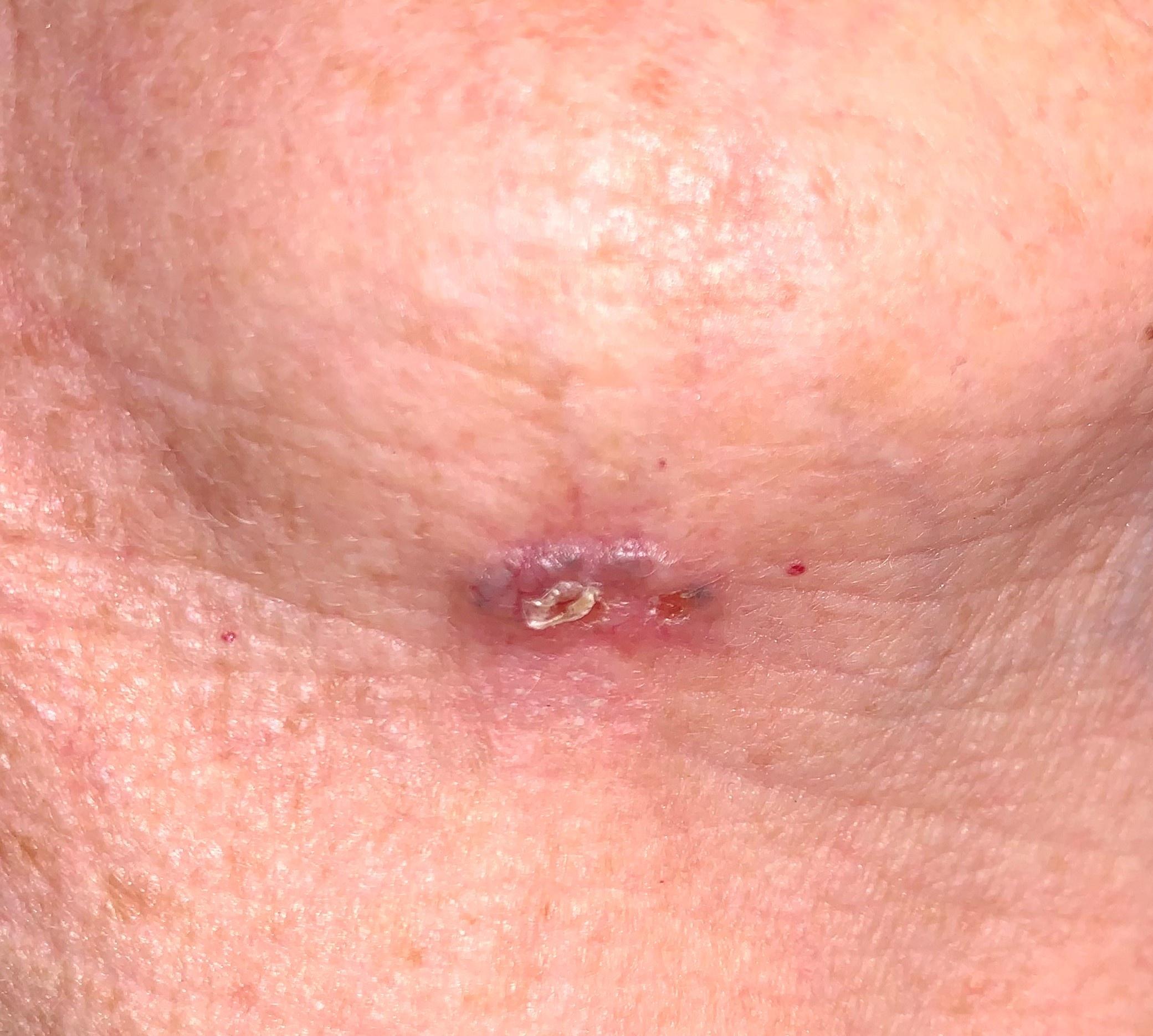<case>
<patient>
<age_approx>75</age_approx>
<sex>female</sex>
</patient>
<image>clinical overview photograph</image>
<lesion_location>
<region>the head or neck</region>
</lesion_location>
<diagnosis>
<name>Basal cell carcinoma</name>
<malignancy>malignant</malignancy>
<confirmation>histopathology</confirmation>
<lineage>adnexal</lineage>
</diagnosis>
</case>